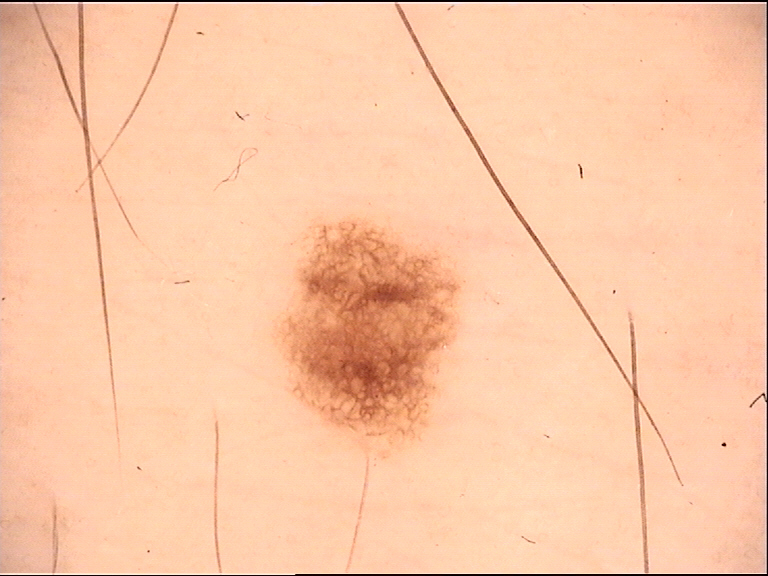Findings:
• class: dysplastic junctional nevus (expert consensus)